The patient is 40–49, female; the affected area is the head or neck; this is a close-up image — 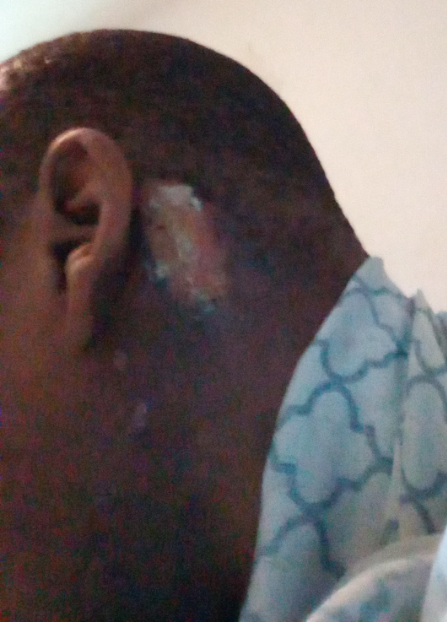Findings:
– dermatologist impression · single-reviewer assessment: in keeping with Cutaneous lupus